Dermoscopy of a skin lesion:
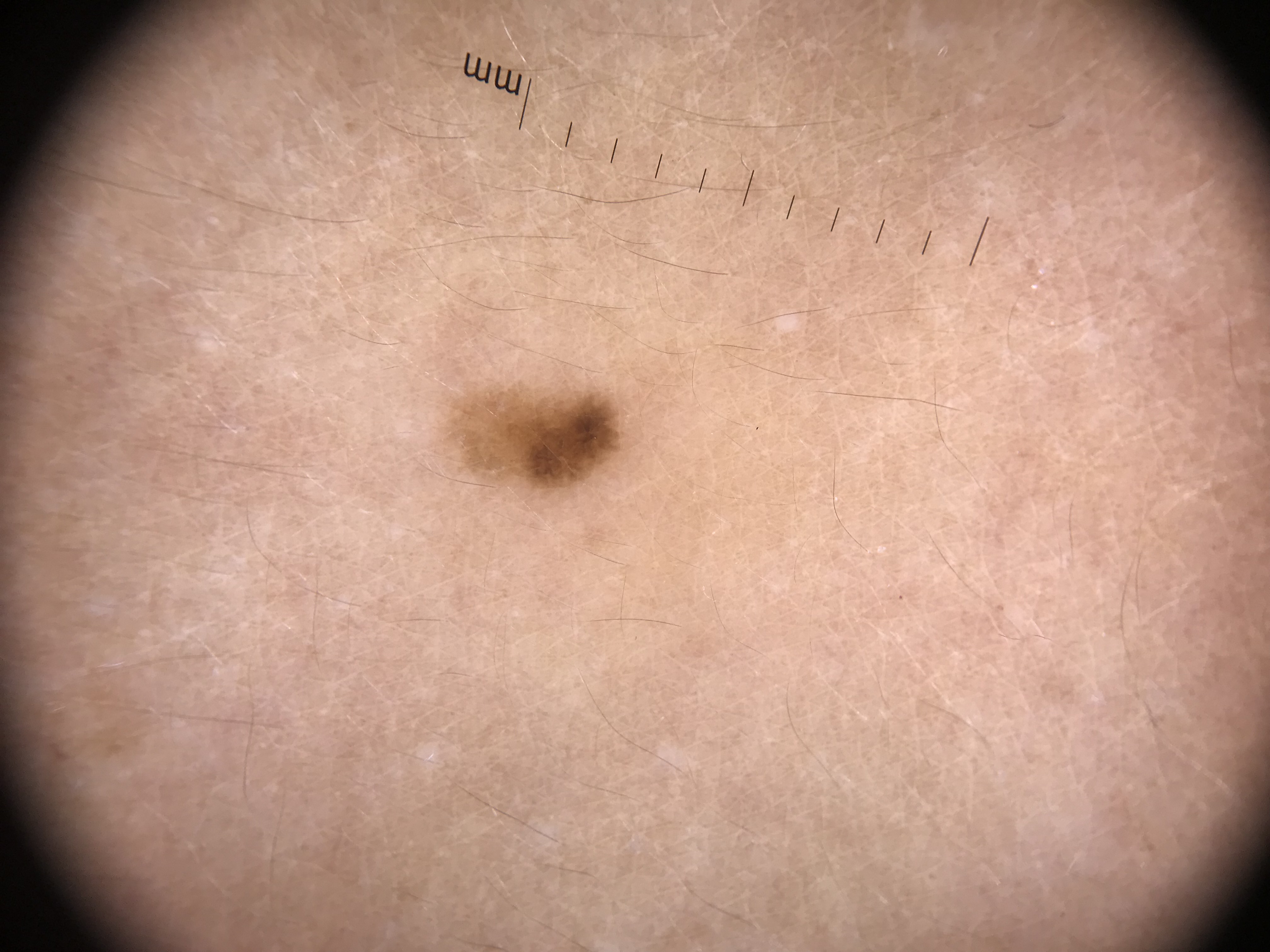Impression: Labeled as a dysplastic junctional nevus.